A dermoscopy image of a single skin lesion.
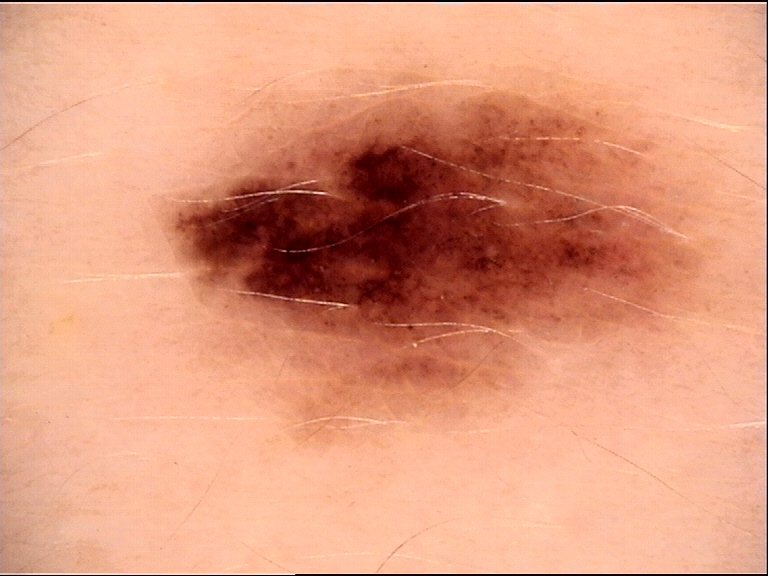Classified as a benign lesion — a dysplastic junctional nevus.